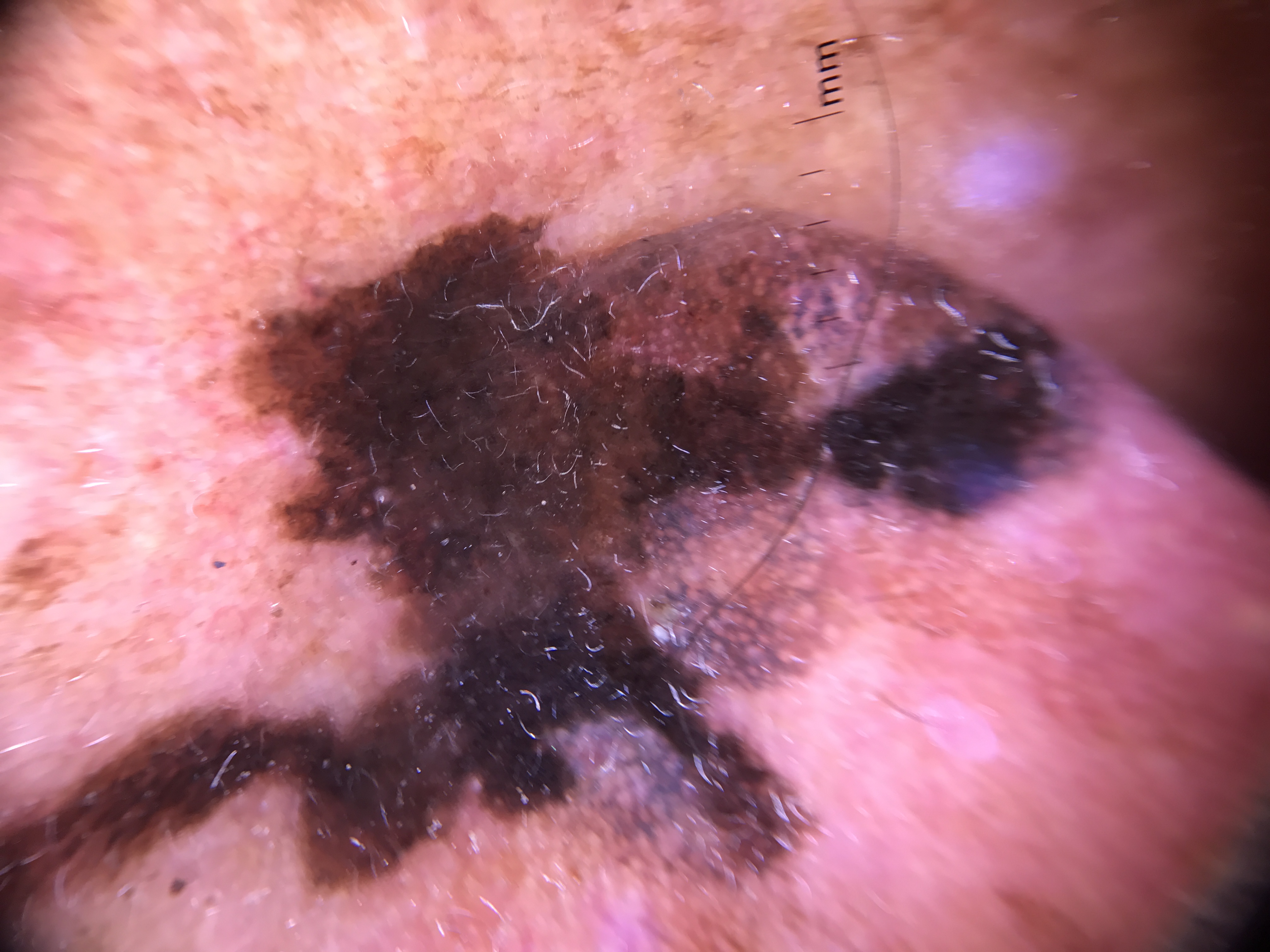The biopsy diagnosis was a lentigo maligna.